This is a close-up image: 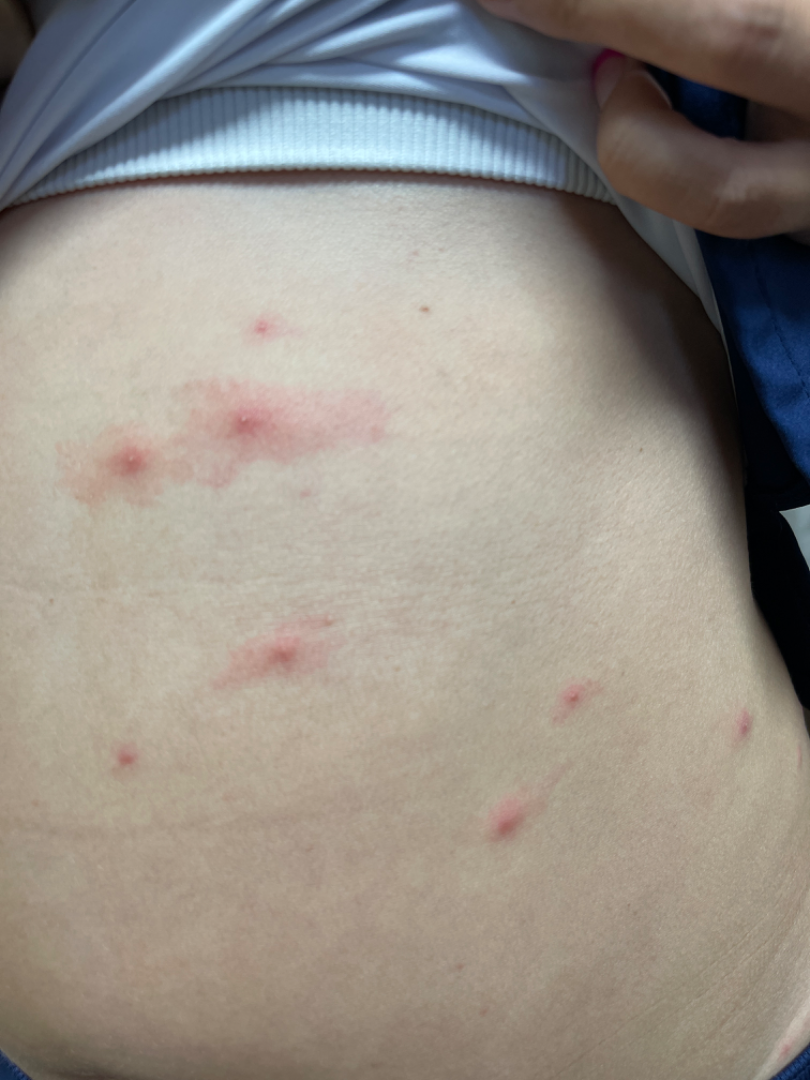diagnostic considerations — Folliculitis (most likely); Insect Bite (considered)